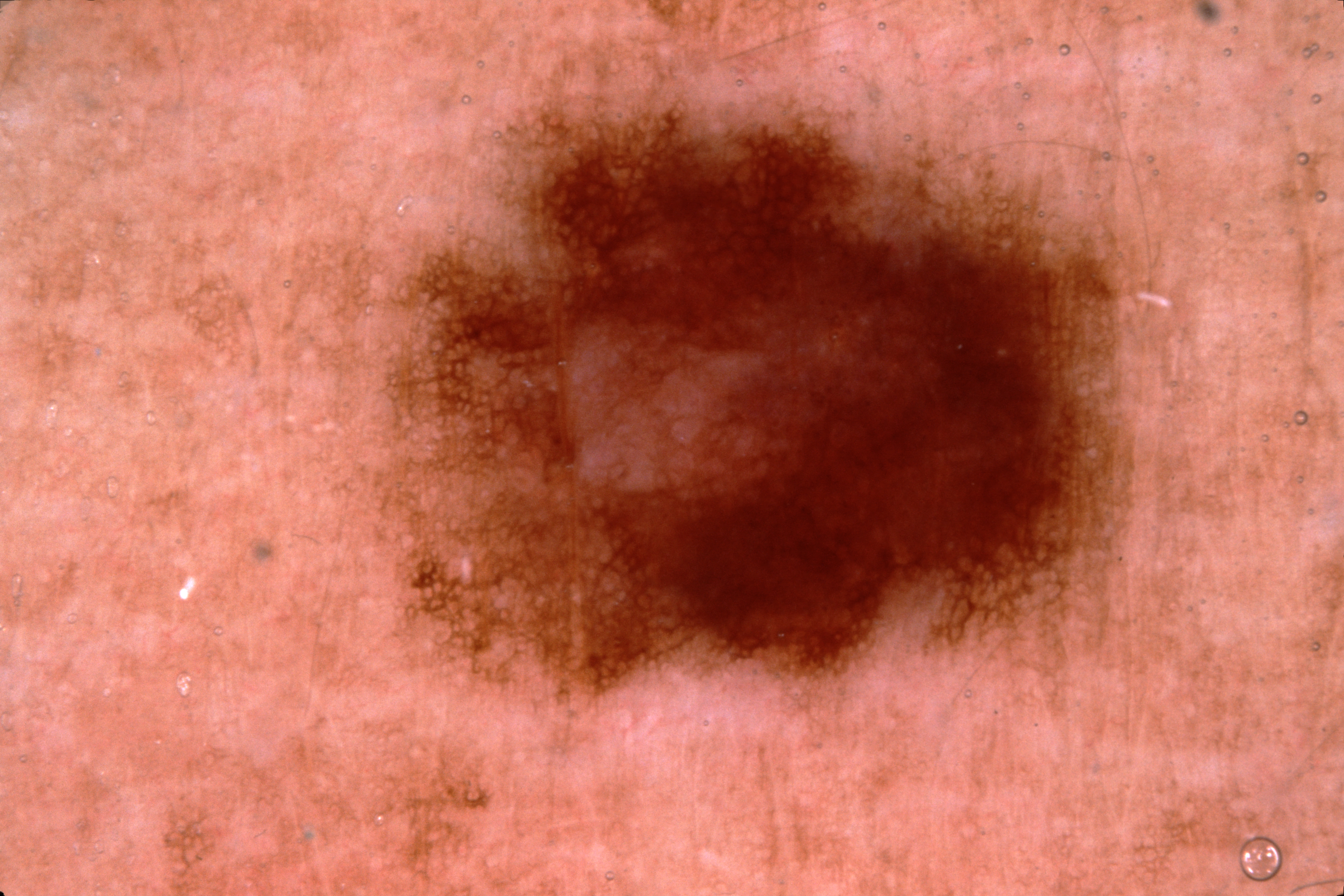A dermoscopic image of a skin lesion.
A male subject, in their 50s.
The lesion covers approximately 37% of the dermoscopic field.
The lesion's extent is left=291, top=0, right=1236, bottom=738.
The lesion extends to the edge of the dermoscopic field.
The dermoscopic pattern shows pigment network.
Diagnosed as a melanocytic nevus.